A skin lesion imaged with a dermatoscope. A male patient in their 70s.
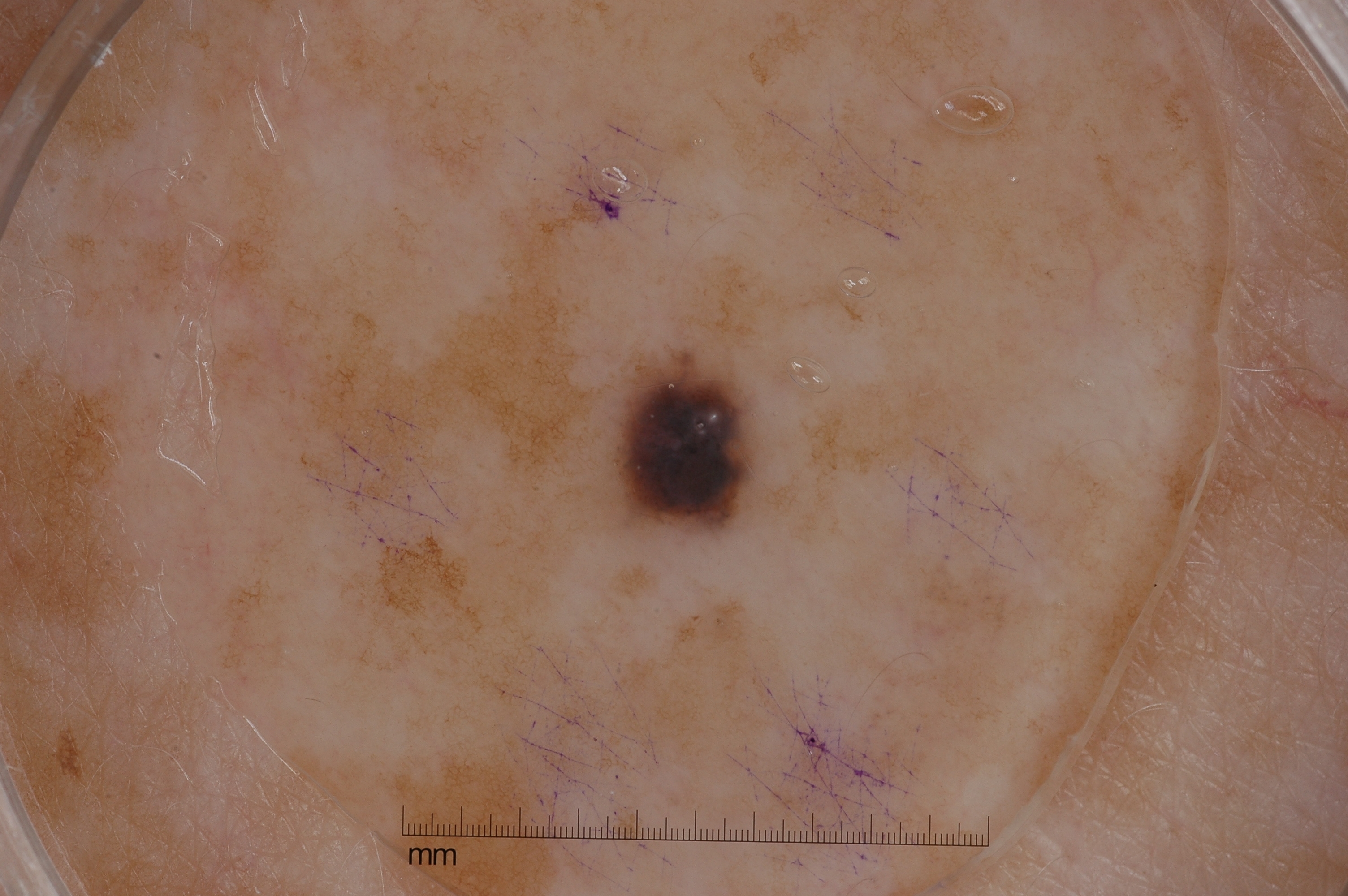Case summary:
With coordinates (x1, y1, x2, y2), the lesion occupies the region 606 349 757 539. The lesion takes up about 2% of the image. Dermoscopically, the lesion shows milia-like cysts.
Assessment:
Clinically diagnosed as a melanocytic nevus.